A dermoscopic image of a skin lesion · a male subject, aged around 15.
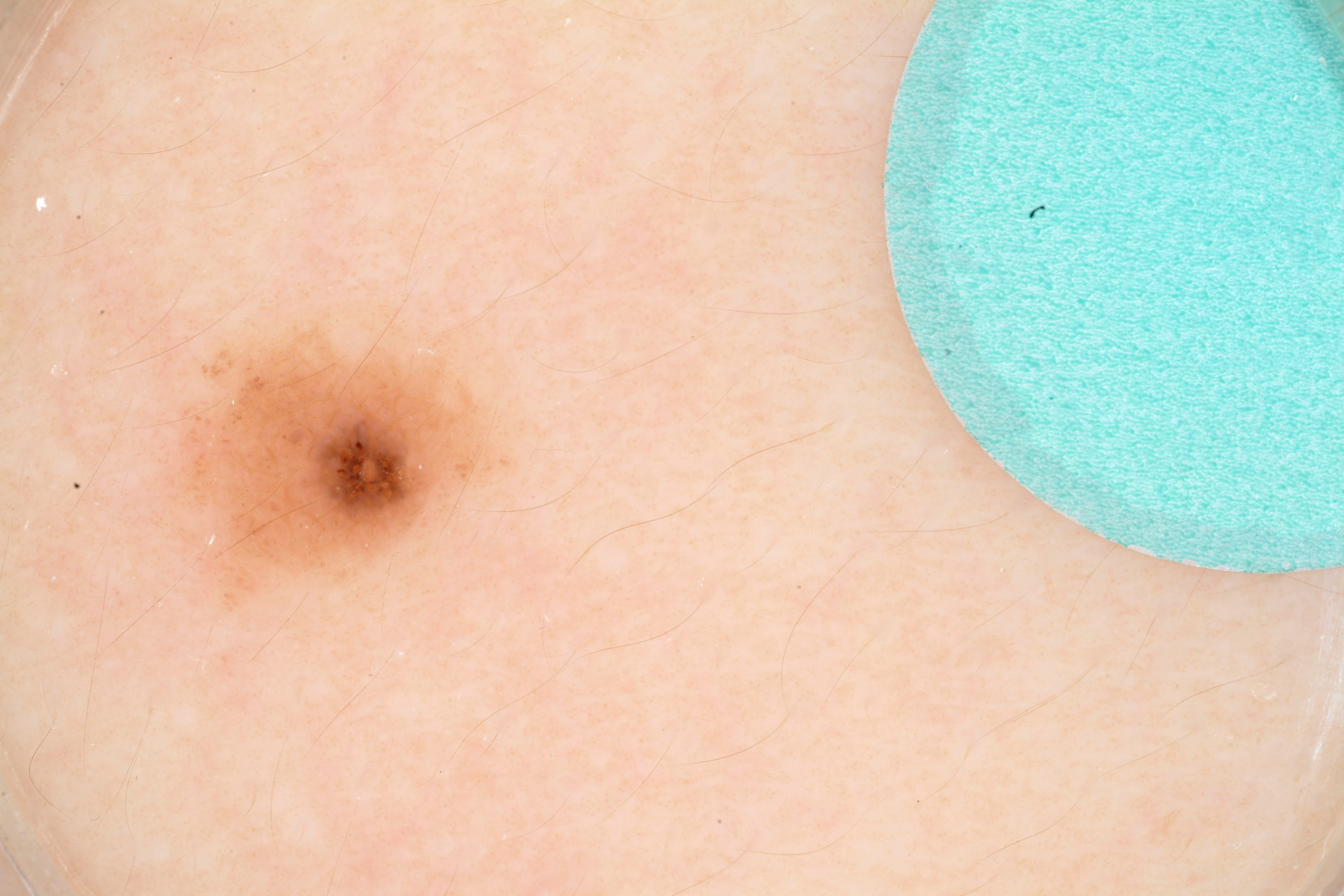Findings:
• features · milia-like cysts; absent: pigment network, globules, negative network, and streaks
• lesion size · ~8% of the field
• bounding box · 150/293/559/613
• impression · a melanocytic nevus